A male patient, aged approximately 30. A dermoscopic view of a skin lesion: 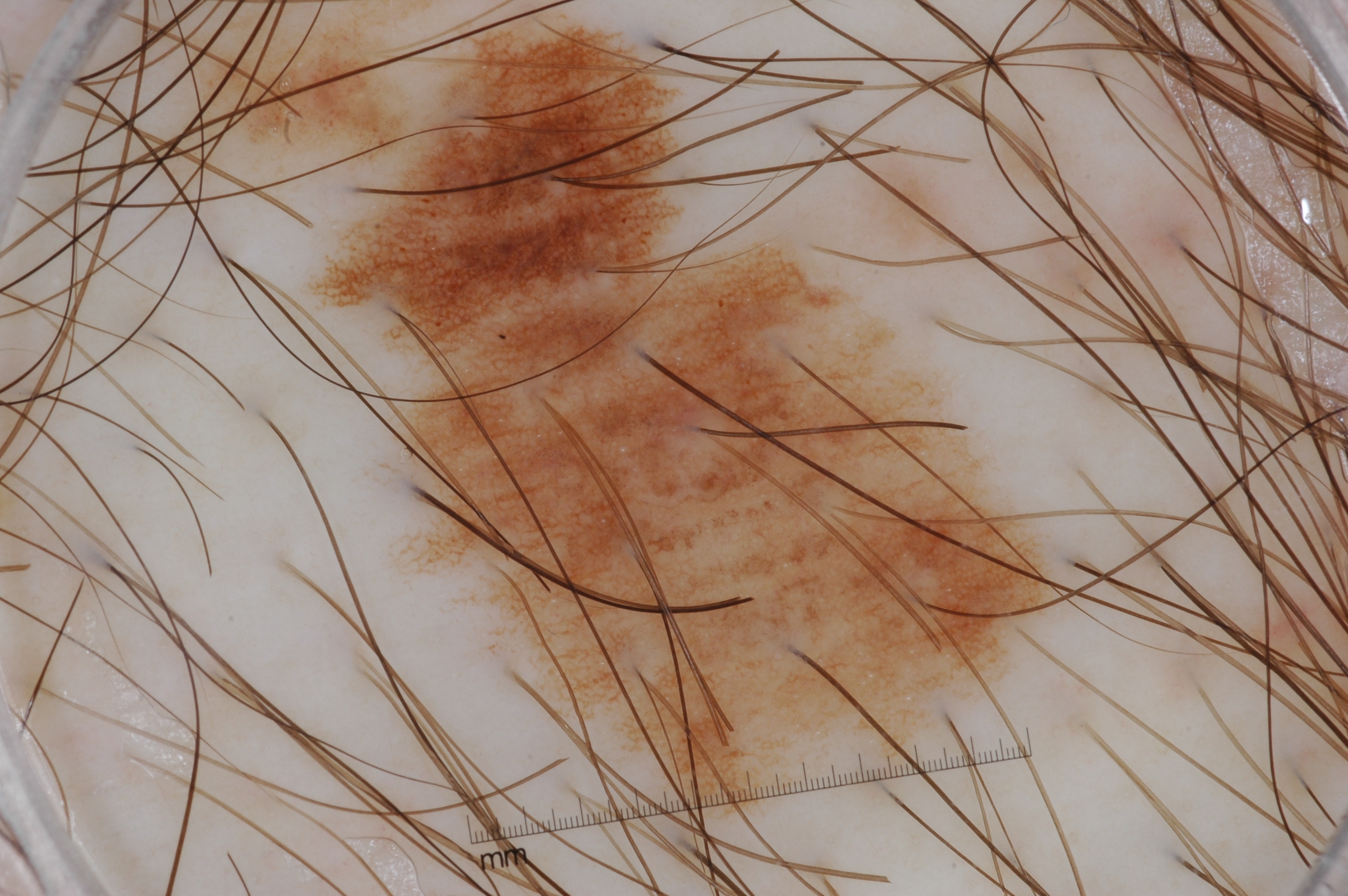lesion bbox — bbox=[327, 28, 1053, 812] | features — pigment network and milia-like cysts | lesion size — ~27% of the field | impression — a melanocytic nevus.